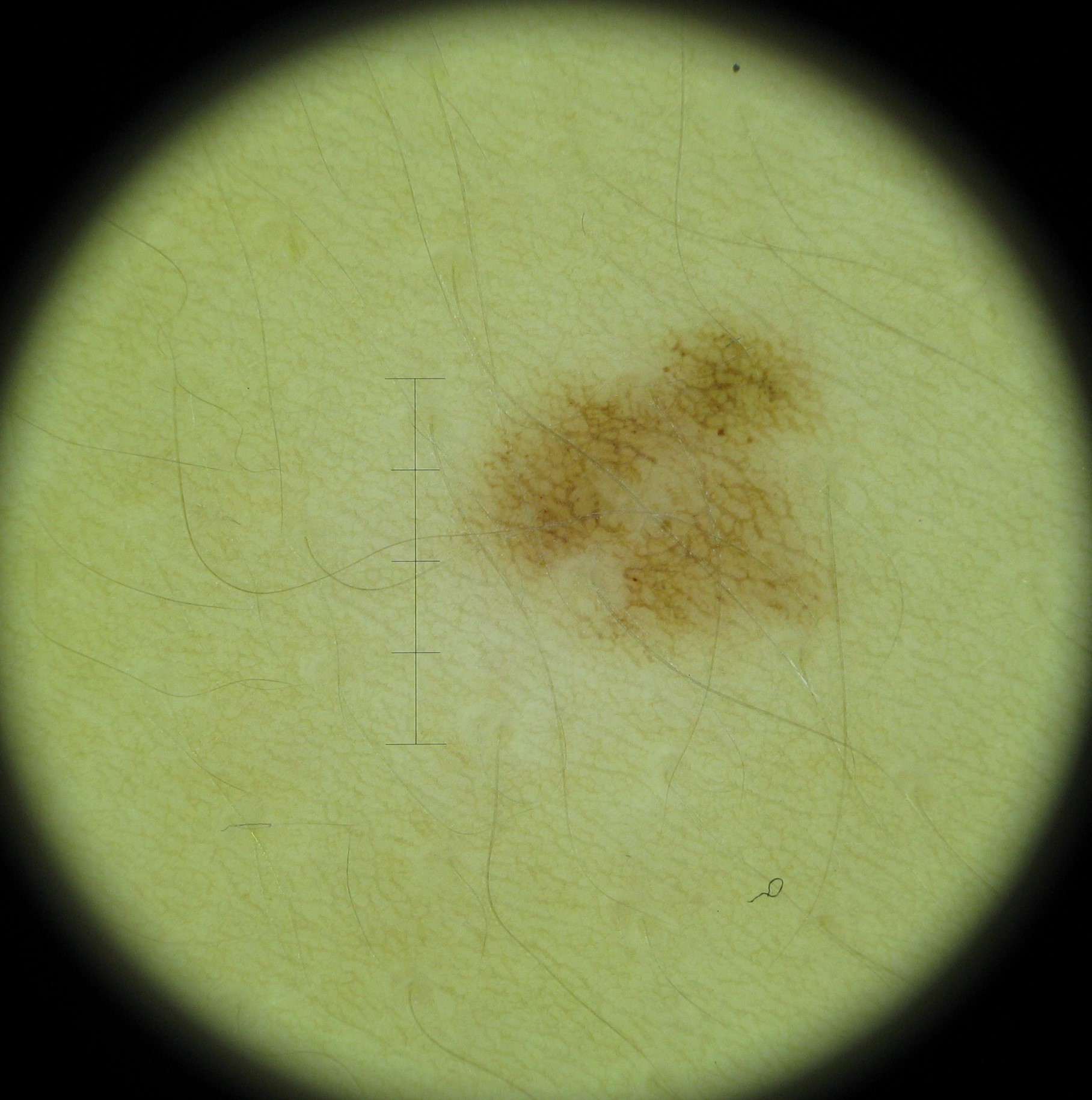Findings:
– diagnostic label: dysplastic junctional nevus (expert consensus)